A male subject 83 years old · imaged for a research study, with no referral diagnosis recorded · a dermatoscopic image of a skin lesion: 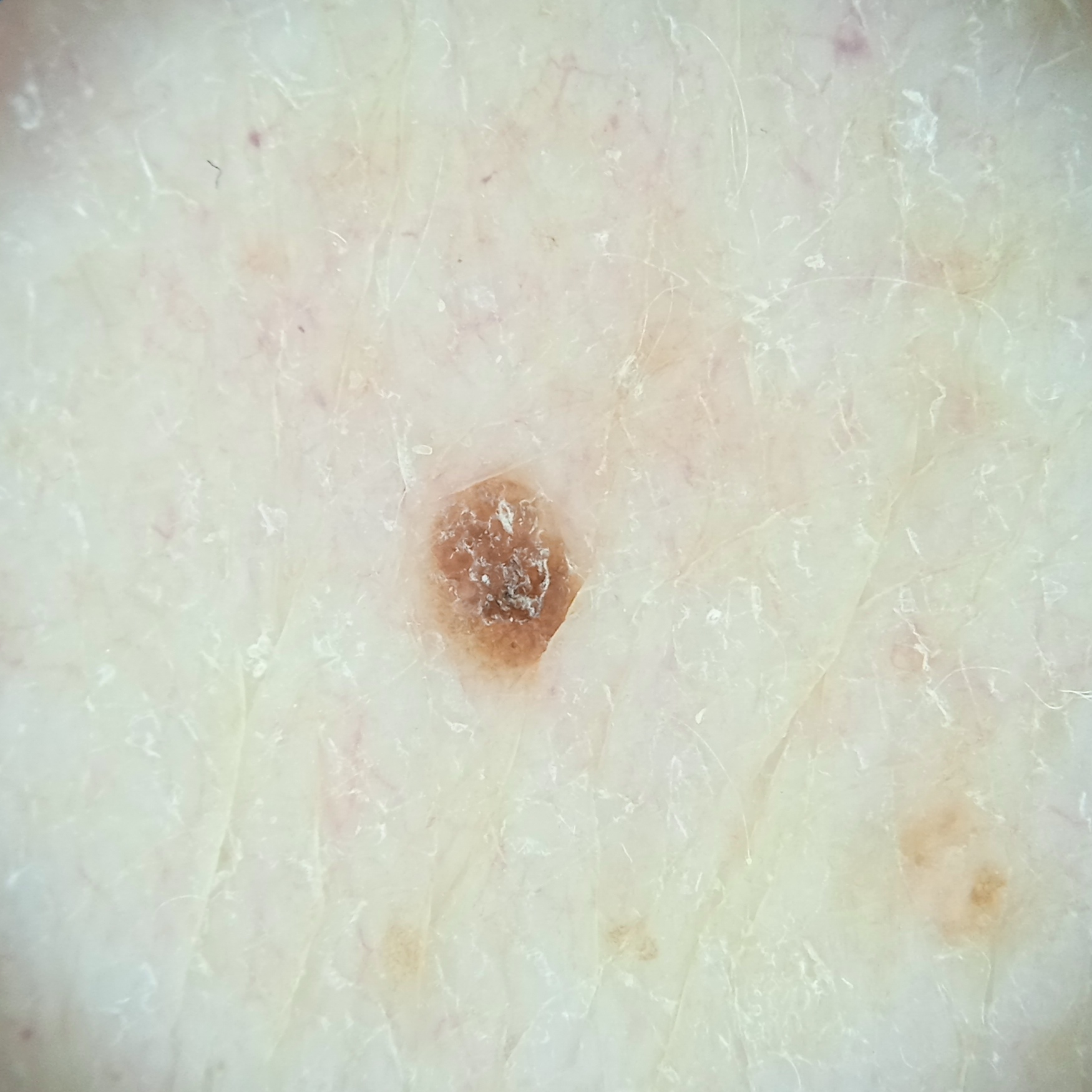{"lesion_size": {"diameter_mm": 2.5}, "diagnosis": {"name": "seborrheic keratosis", "malignancy": "benign"}}